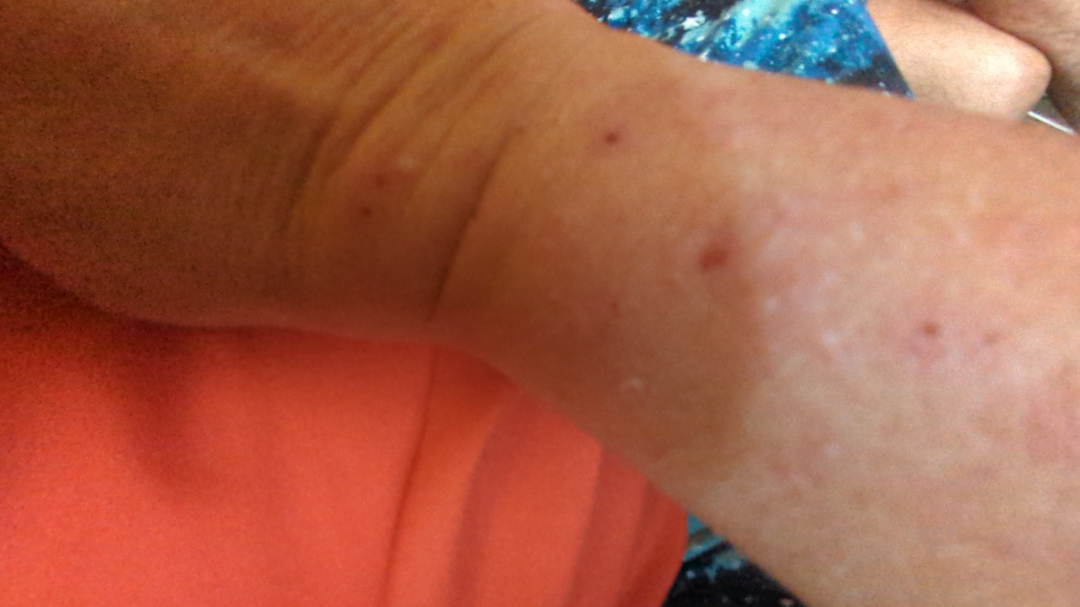Background: Symptoms reported: itching. The head or neck, arm and leg are involved. The condition has been present for more than one year. Texture is reported as raised or bumpy. The contributor is 50–59, female. The patient described the issue as a rash. An image taken at an angle. The contributor notes associated joint pain, fatigue, shortness of breath and fever. Findings: Three dermatologists each reviewed the case: the favored diagnosis is Prurigo nodularis; an alternative is Inflicted skin lesions; also on the differential is Actinic Keratosis; a more distant consideration is Skin infection.